The chart notes pesticide exposure, prior malignancy (patient or family), and no tobacco use; a clinical close-up photograph of a skin lesion; a male subject in their 60s; the patient was assessed as Fitzpatrick II: 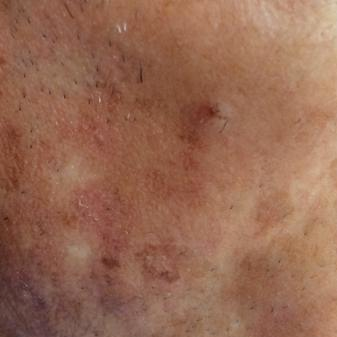Q: What is the anatomic site?
A: the face
Q: Lesion size?
A: approx. 35 × 15 mm
Q: Any reported symptoms?
A: itching / no pain, no change in appearance
Q: What is this lesion?
A: actinic keratosis (clinical consensus)